A skin lesion imaged with a dermatoscope:
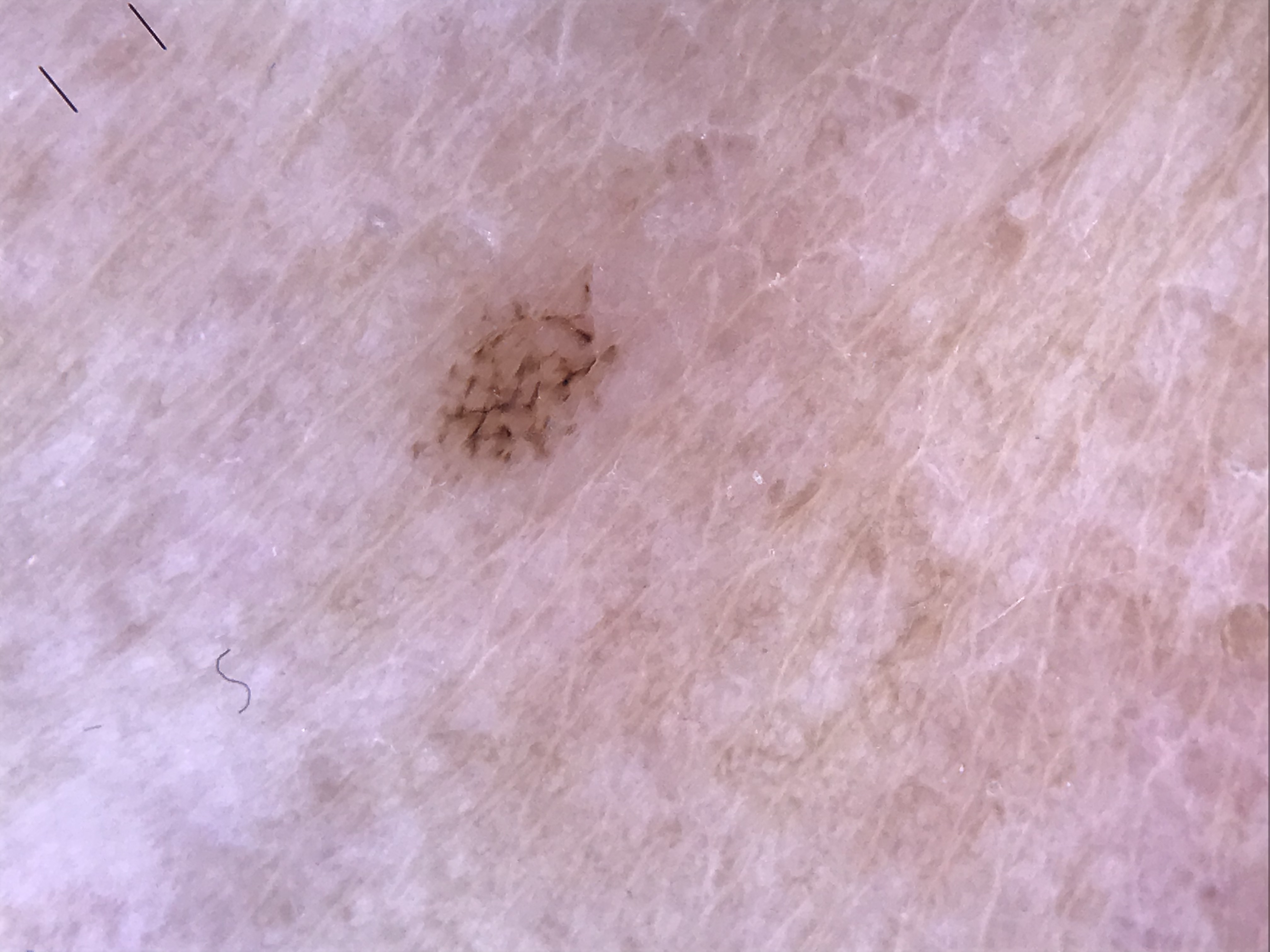Classified as an acral dysplastic junctional nevus.